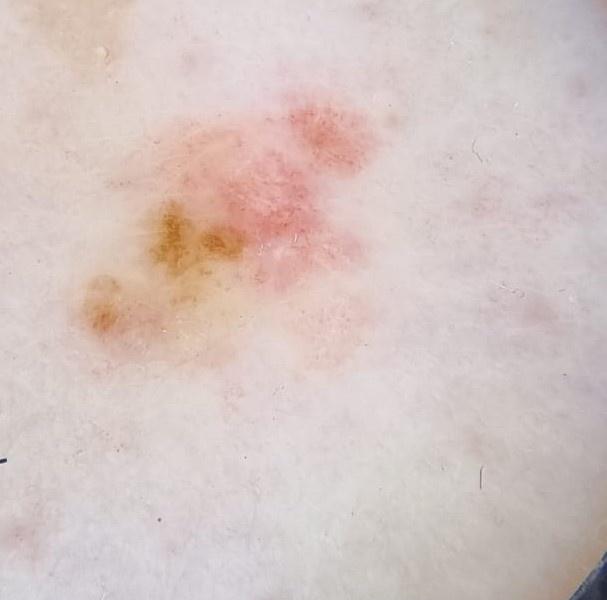Findings: A skin lesion imaged with contact-polarized dermoscopy. The patient is Fitzpatrick phototype II. A female patient aged approximately 85 or older. The lesion was found on a lower extremity. Diagnosis: Histopathology confirmed a malignant lesion — a melanoma.